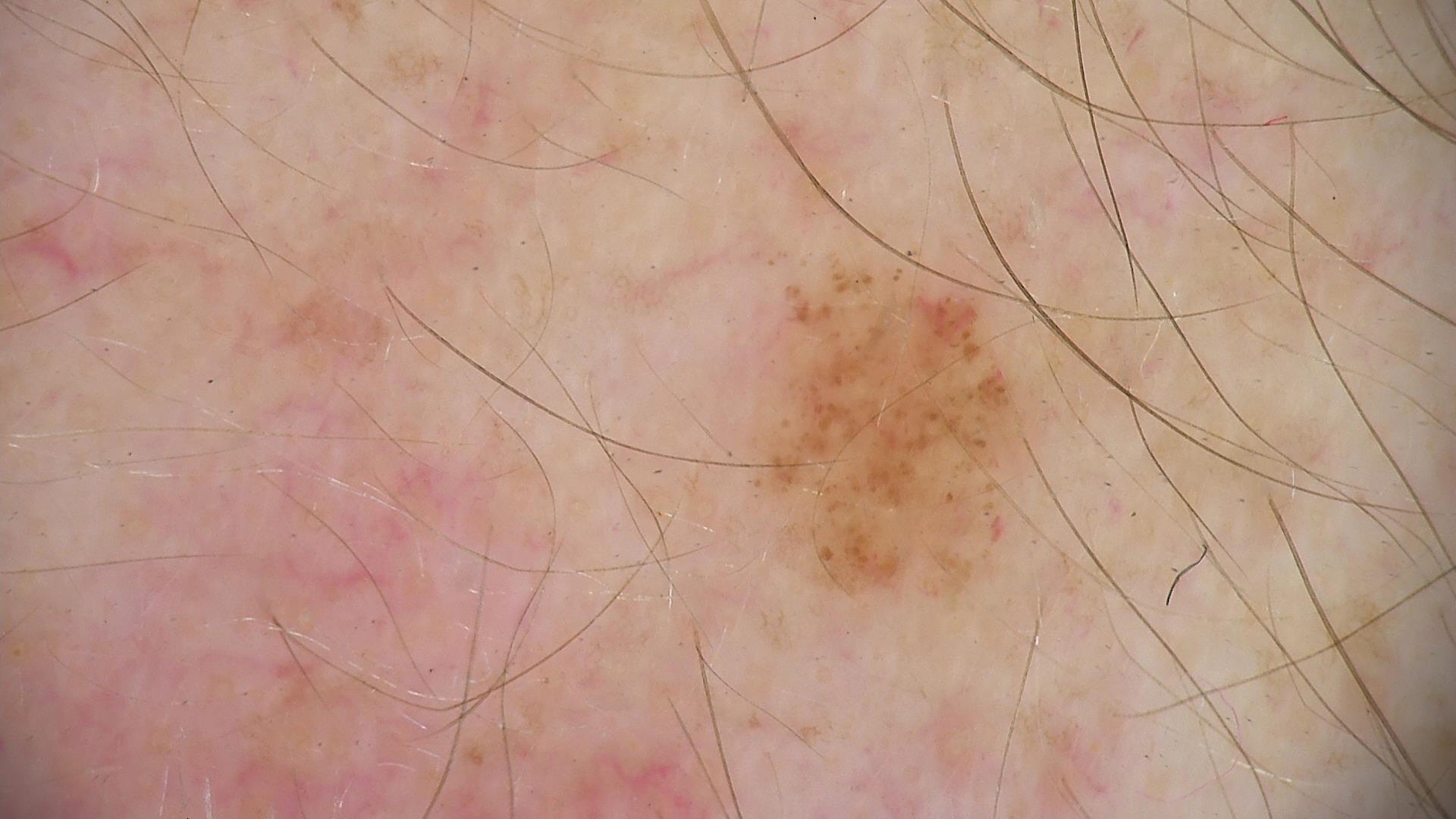assessment=dysplastic junctional nevus (expert consensus).